A dermoscopic photograph of a skin lesion.
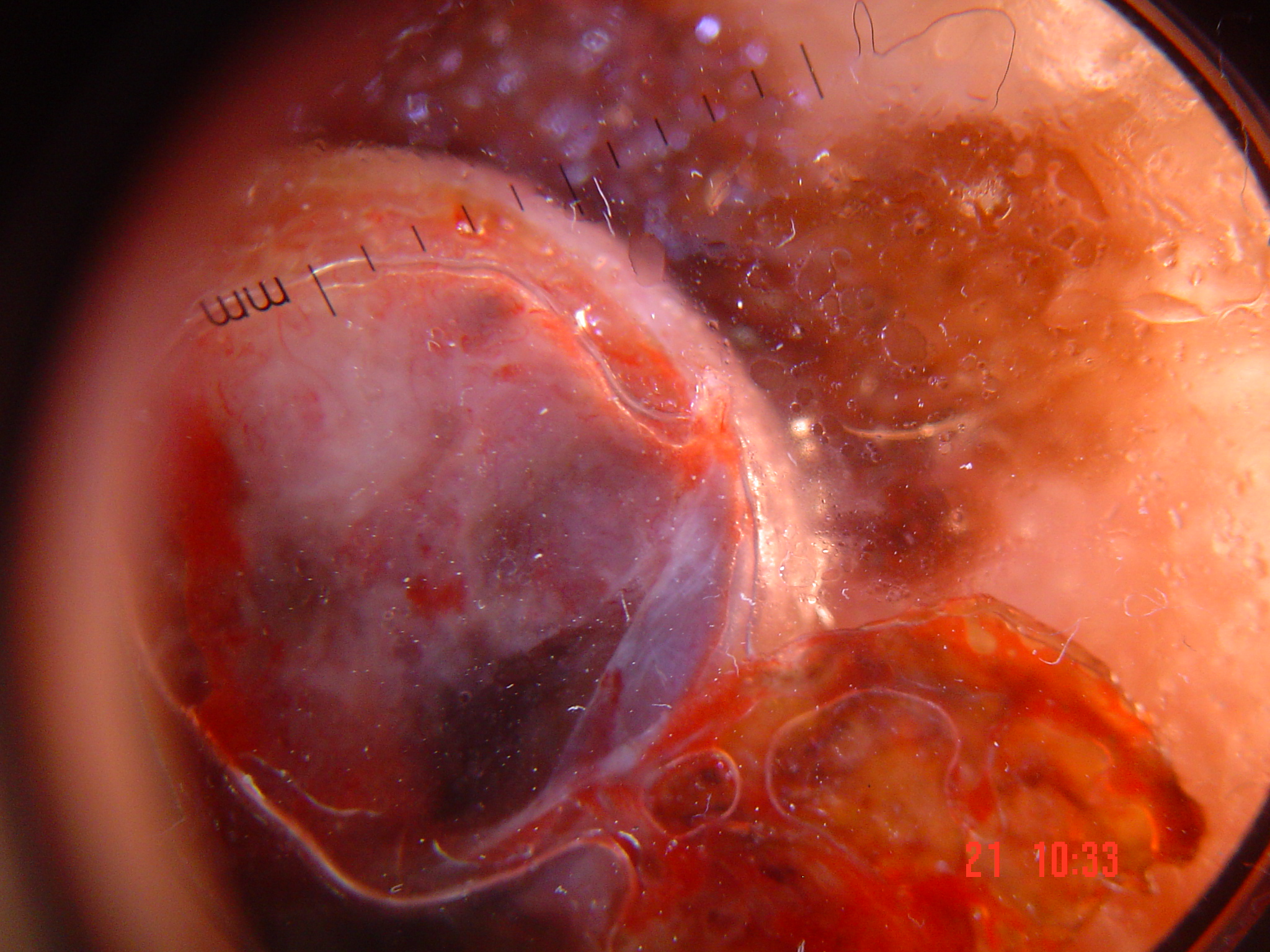Histopathologically confirmed as a lentigo maligna melanoma.